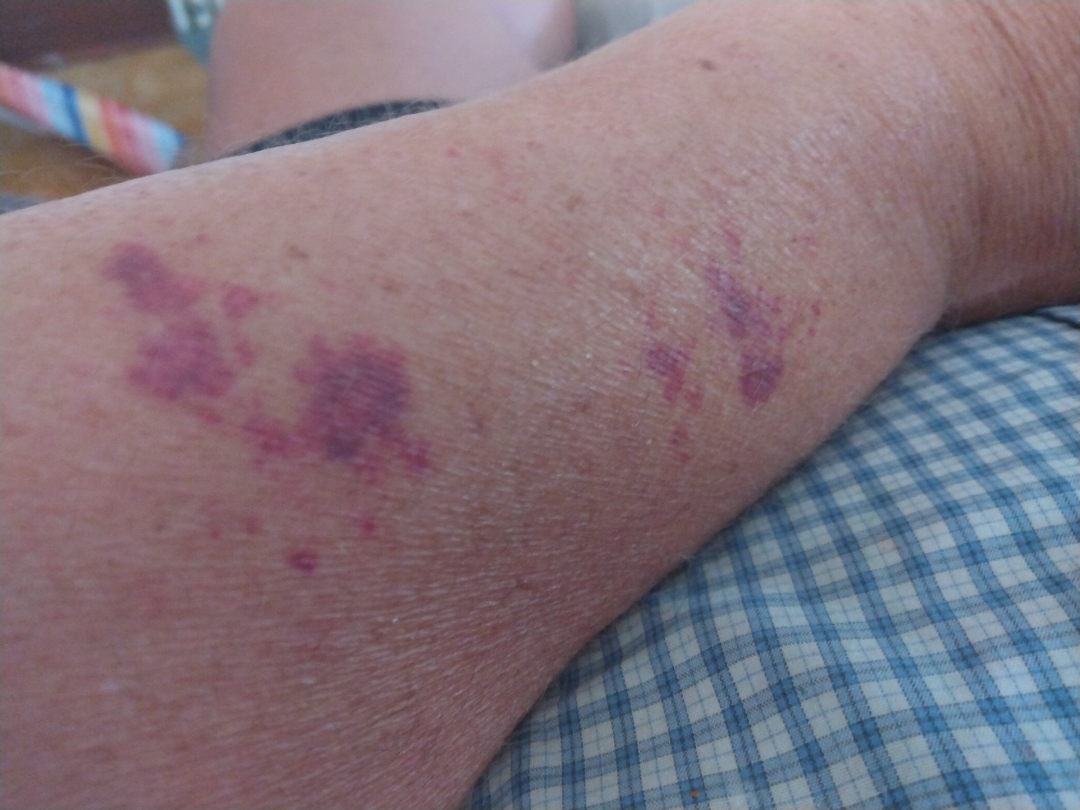The image was not sufficient for the reviewer to characterize the skin condition.
The lesion involves the arm.
This image was taken at an angle.